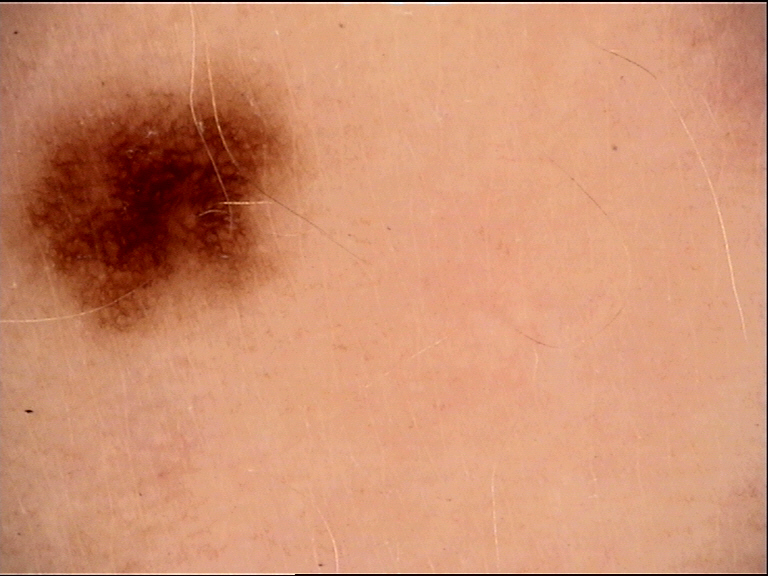Conclusion:
Diagnosed as a dysplastic junctional nevus.